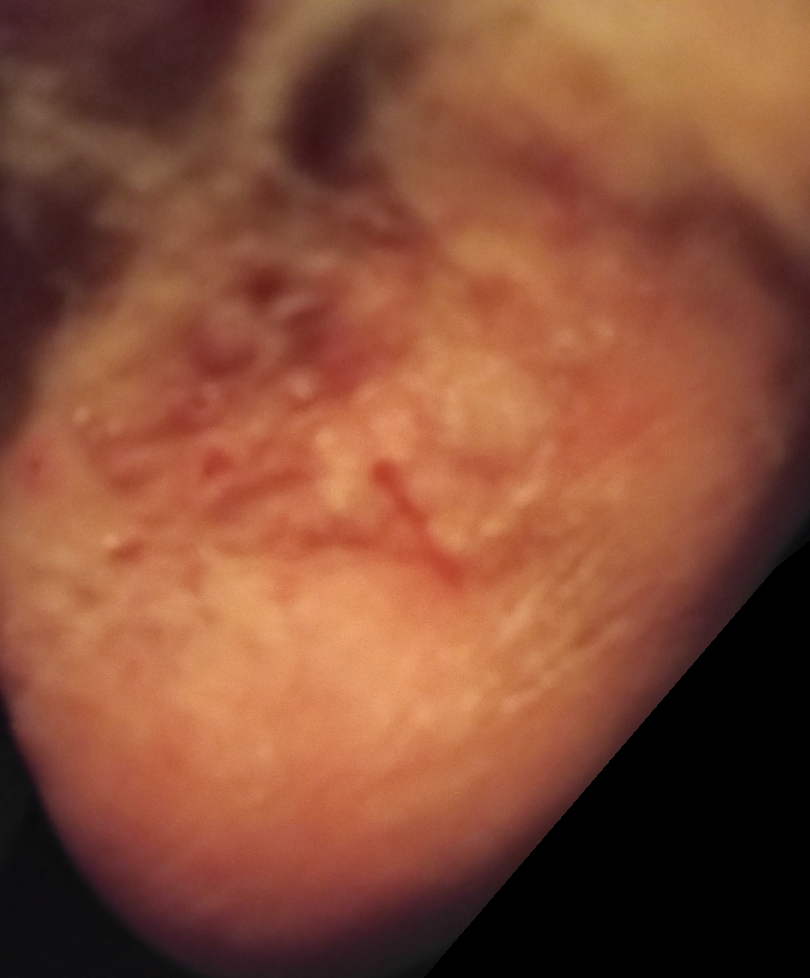The skin condition could not be confidently assessed from this image.
The patient considered this a rash.
The lesion involves the back of the hand, top or side of the foot and leg.
Male patient, age 50–59.
The lesion is associated with pain, enlargement, bleeding, itching and burning.
The condition has been present for more than one year.
This is a close-up image.